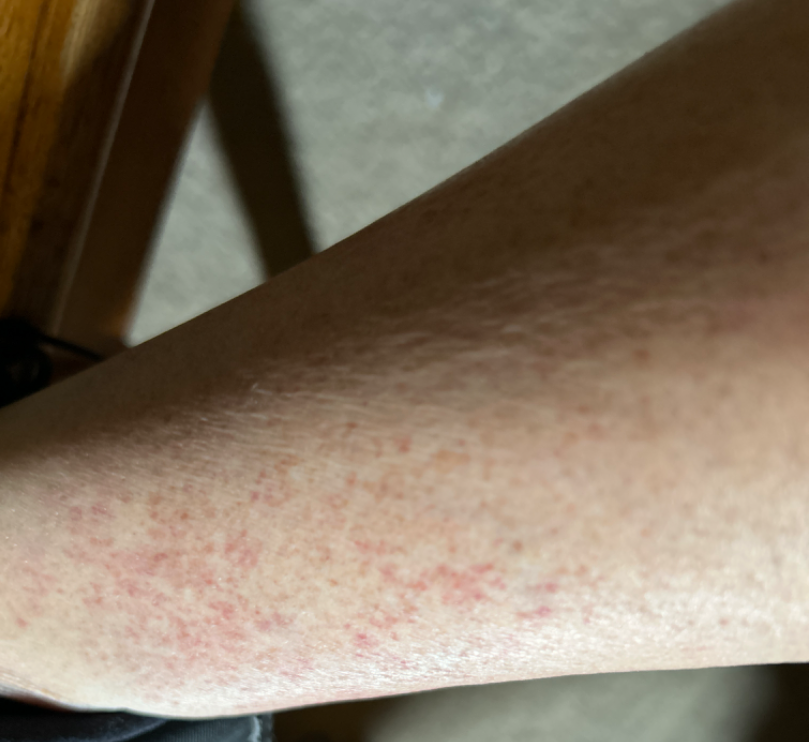{"symptoms": "none reported", "systemic_symptoms": ["fatigue", "joint pain", "fever"], "duration": "less than one week", "skin_tone": {"fitzpatrick": "III", "monk_skin_tone": [2, 3]}, "shot_type": "at an angle", "patient_category": "a rash", "patient": "female, age 40–49", "body_site": "leg", "differential": {"tied_lead": ["Pigmented purpuric eruption", "Leukocytoclastic Vasculitis"]}}